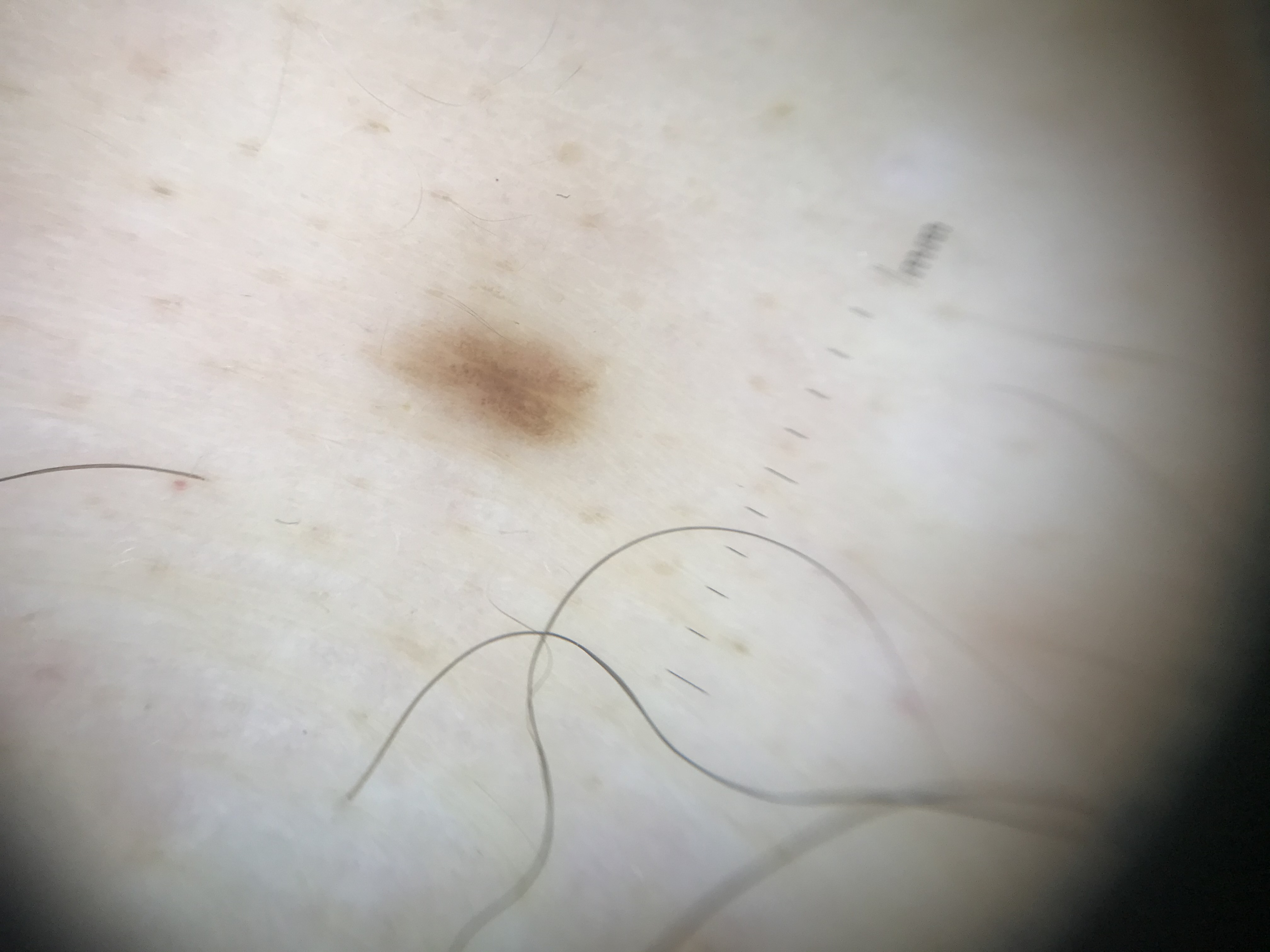Consistent with a junctional nevus.